By self-report, a personal history of cancer · a male patient 65 years of age · a dermatoscopic image of a skin lesion · the referring clinician suspected basal cell carcinoma · the patient says their skin tans without first burning — 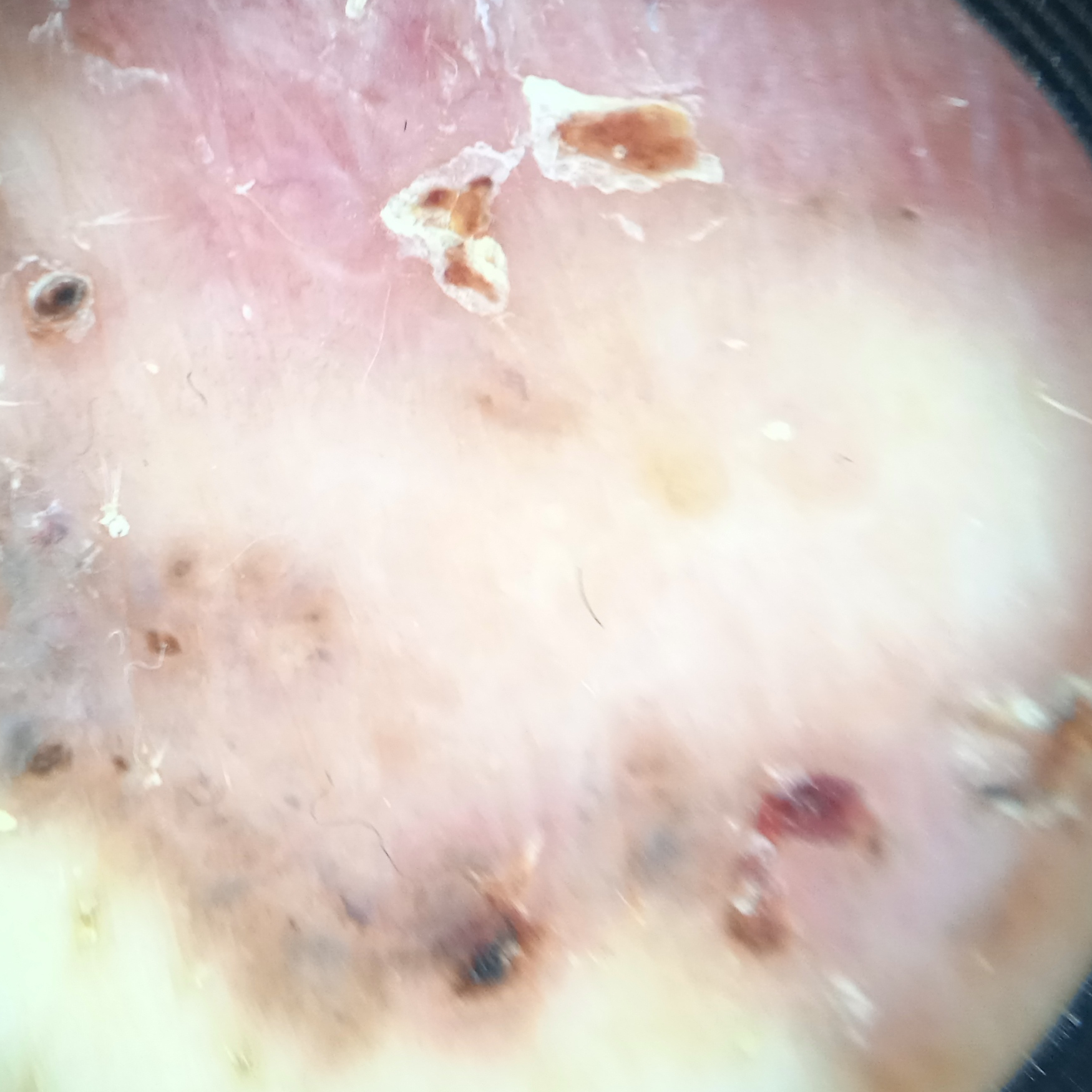anatomic site — the torso
diameter — 66 mm
diagnosis — basal cell carcinoma (biopsy-proven)